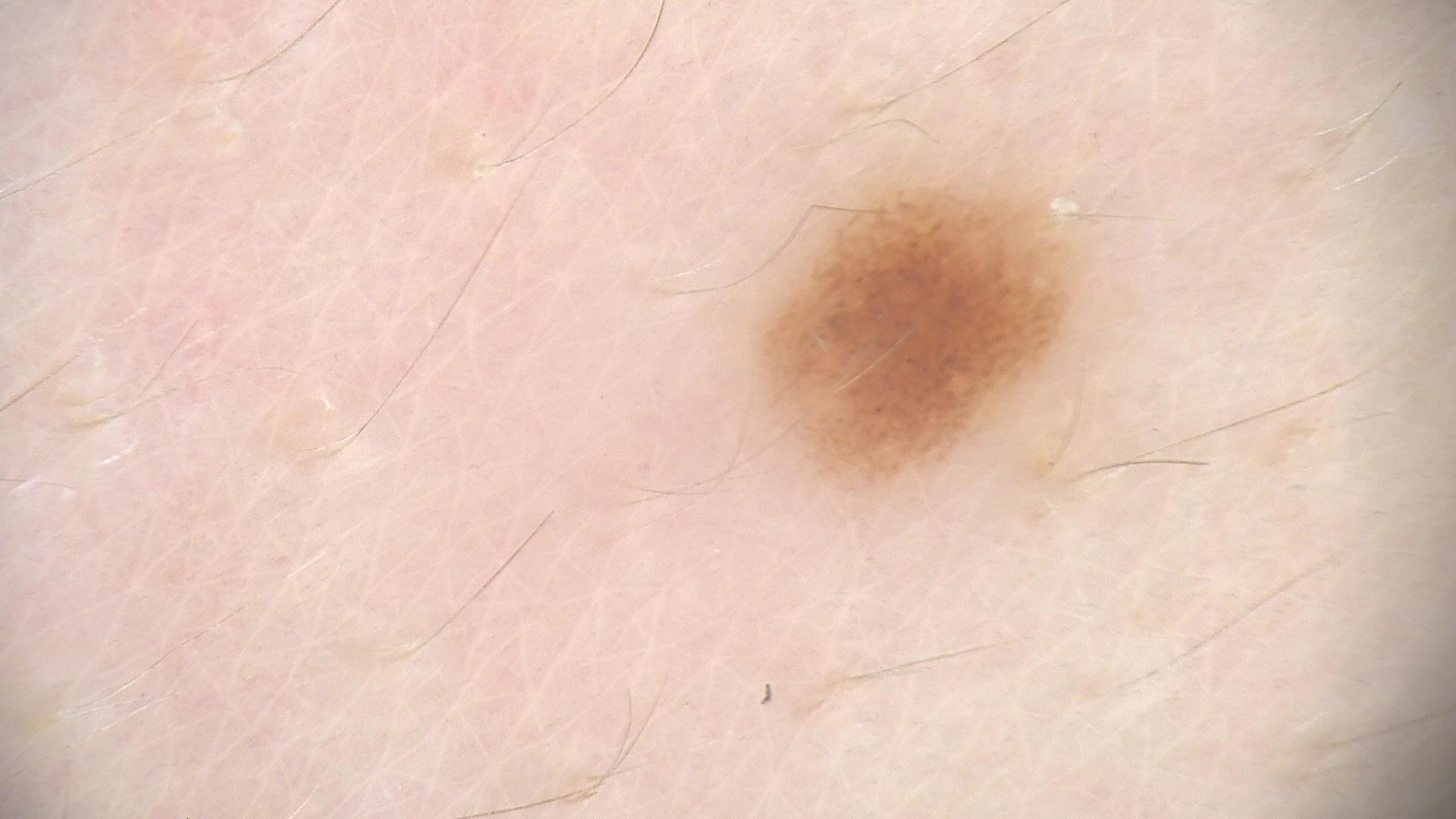modality: dermatoscopy
assessment: dysplastic junctional nevus (expert consensus)